Contact-polarized dermoscopy of a skin lesion; a female patient aged approximately 30; the patient is FST II: 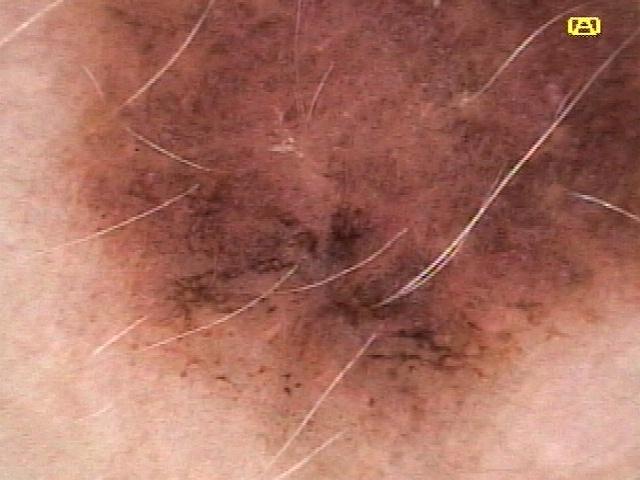Biopsy-confirmed as a melanoma.